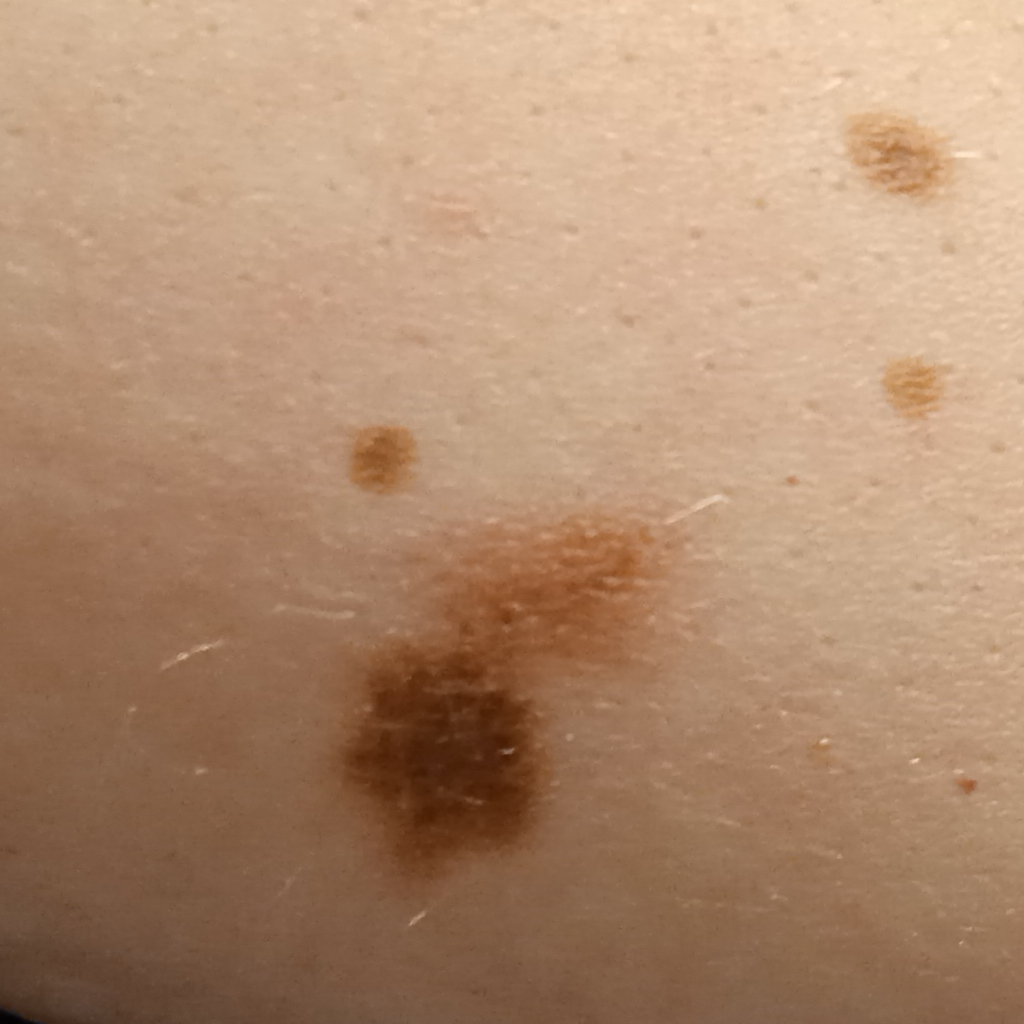Clinical context: A clinical close-up of a skin lesion. A female subject 54 years of age. By self-report, a personal history of cancer, a family history of skin cancer, a personal history of skin cancer, and no immunosuppression. Imaged for a research study, with no referral diagnosis recorded. The lesion measures approximately 17.5 mm. Impression: The dermatologists' assessment was a melanoma.